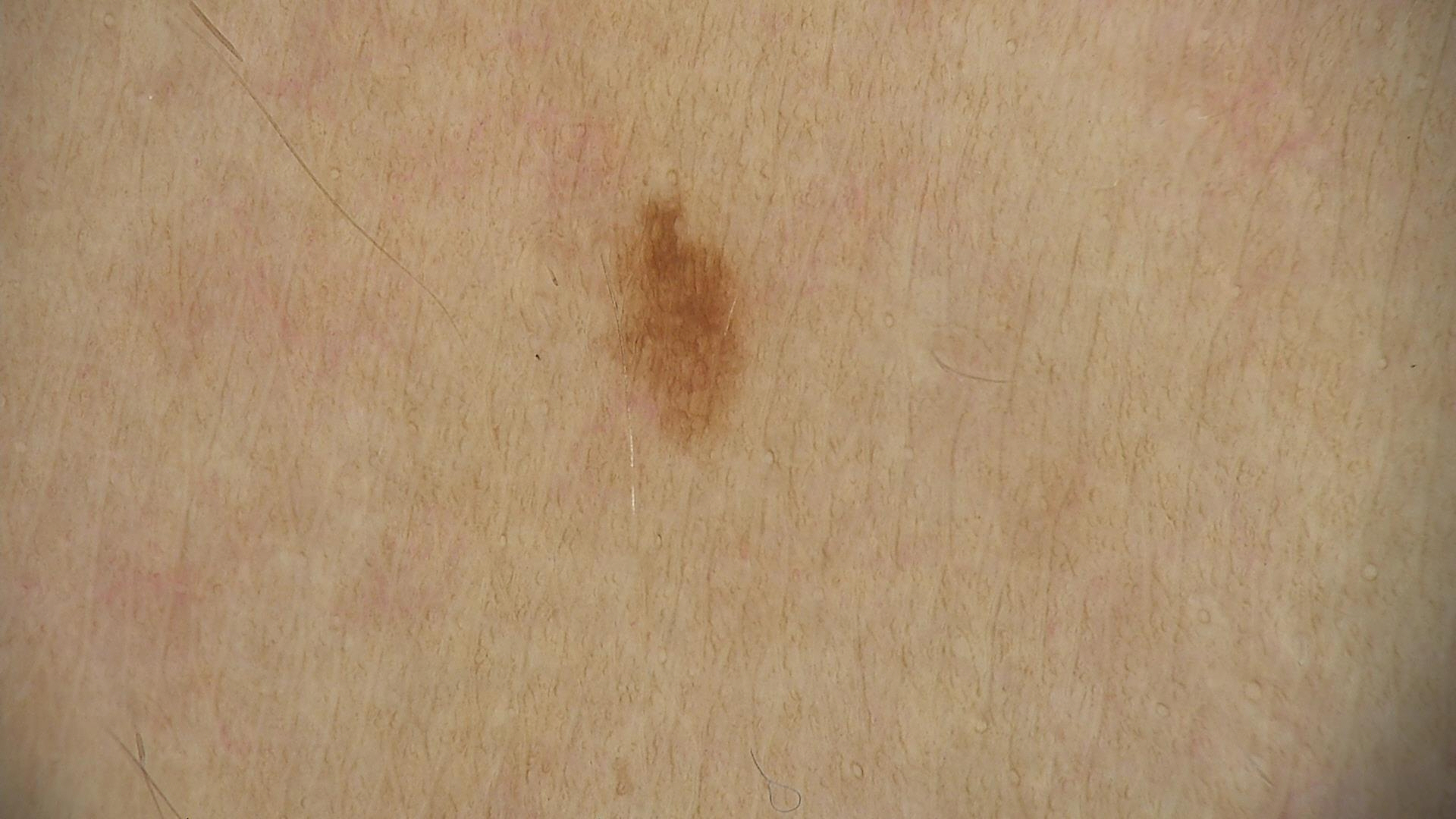Impression:
Labeled as a junctional nevus.